The subject is a female aged approximately 30; a skin lesion imaged with a dermatoscope — 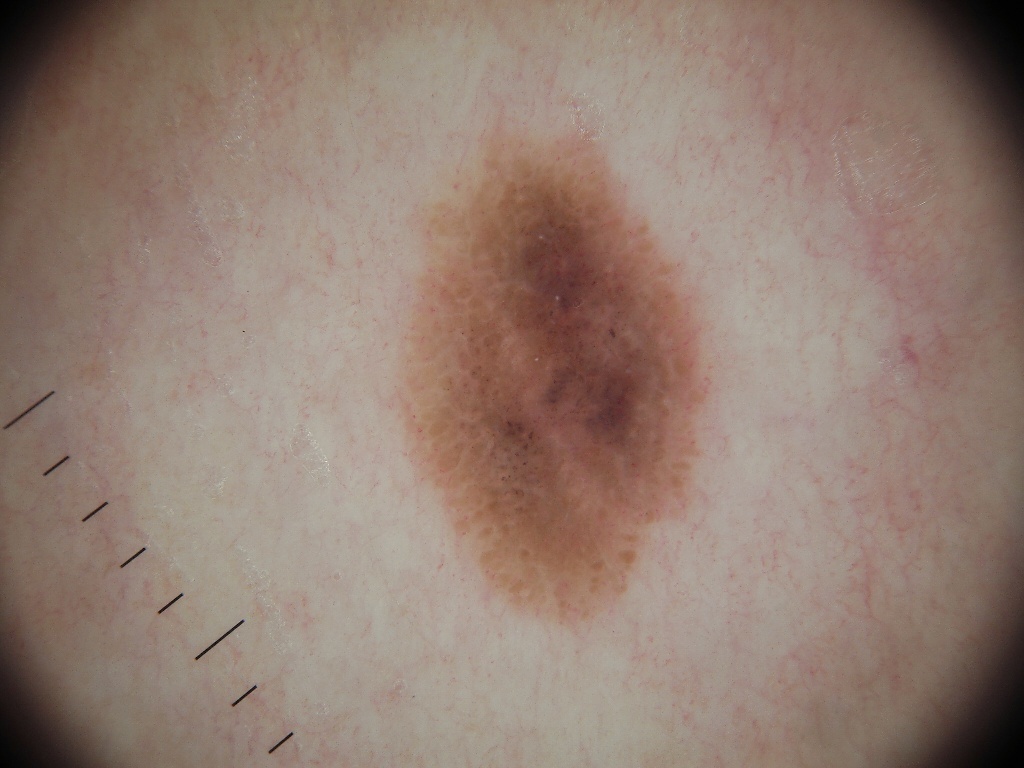lesion_extent:
  approx_field_fraction_pct: 15
dermoscopic_features:
  present:
    - globules
    - negative network
    - milia-like cysts
  absent:
    - streaks
    - pigment network
lesion_location:
  bbox_xyxy:
    - 395
    - 95
    - 718
    - 629
diagnosis:
  name: melanocytic nevus
  malignancy: benign
  lineage: melanocytic
  provenance: clinical